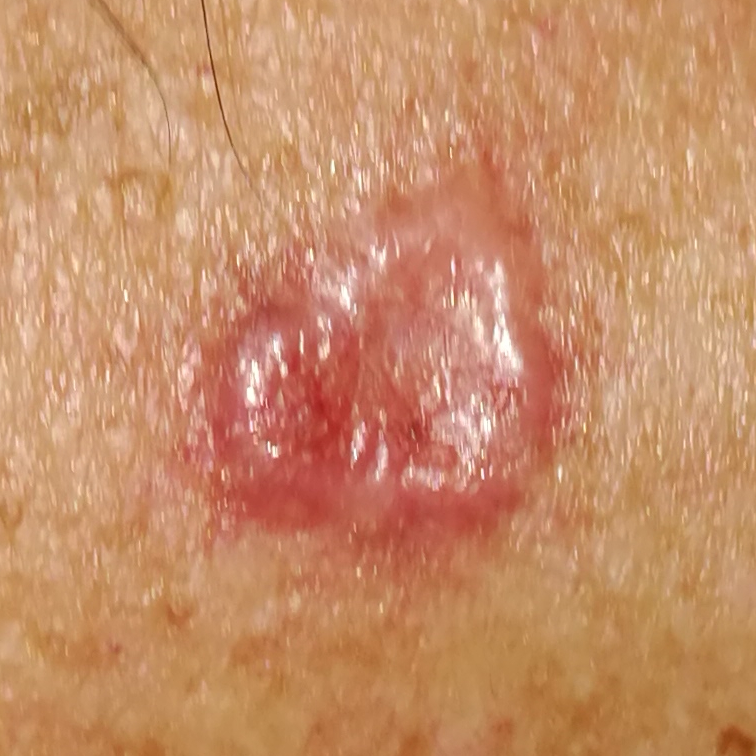{
  "skin_type": "III",
  "lesion_location": "the back",
  "lesion_size": {
    "diameter_1_mm": 13.0,
    "diameter_2_mm": 12.0
  },
  "symptoms": {
    "present": [
      "itching",
      "growth",
      "elevation"
    ]
  },
  "diagnosis": {
    "name": "basal cell carcinoma",
    "code": "BCC",
    "malignancy": "malignant",
    "confirmation": "histopathology"
  }
}